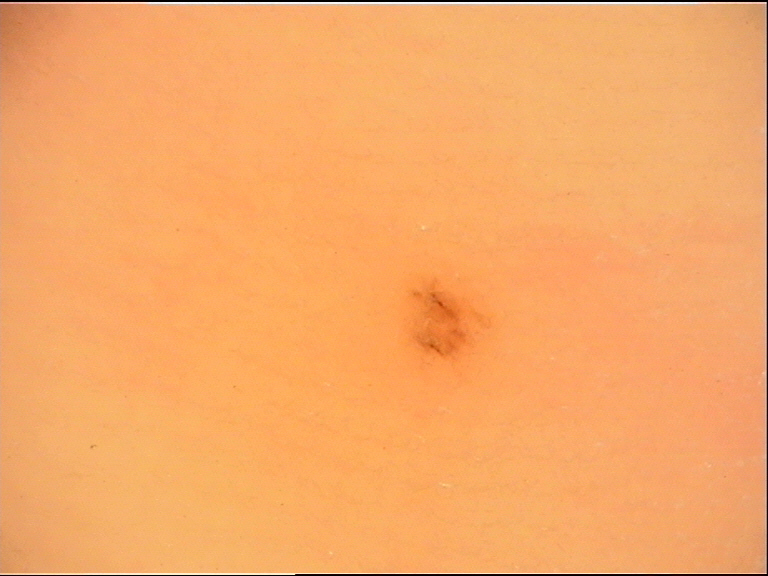Impression: Classified as an acral junctional nevus.